A dermoscopic close-up of a skin lesion:
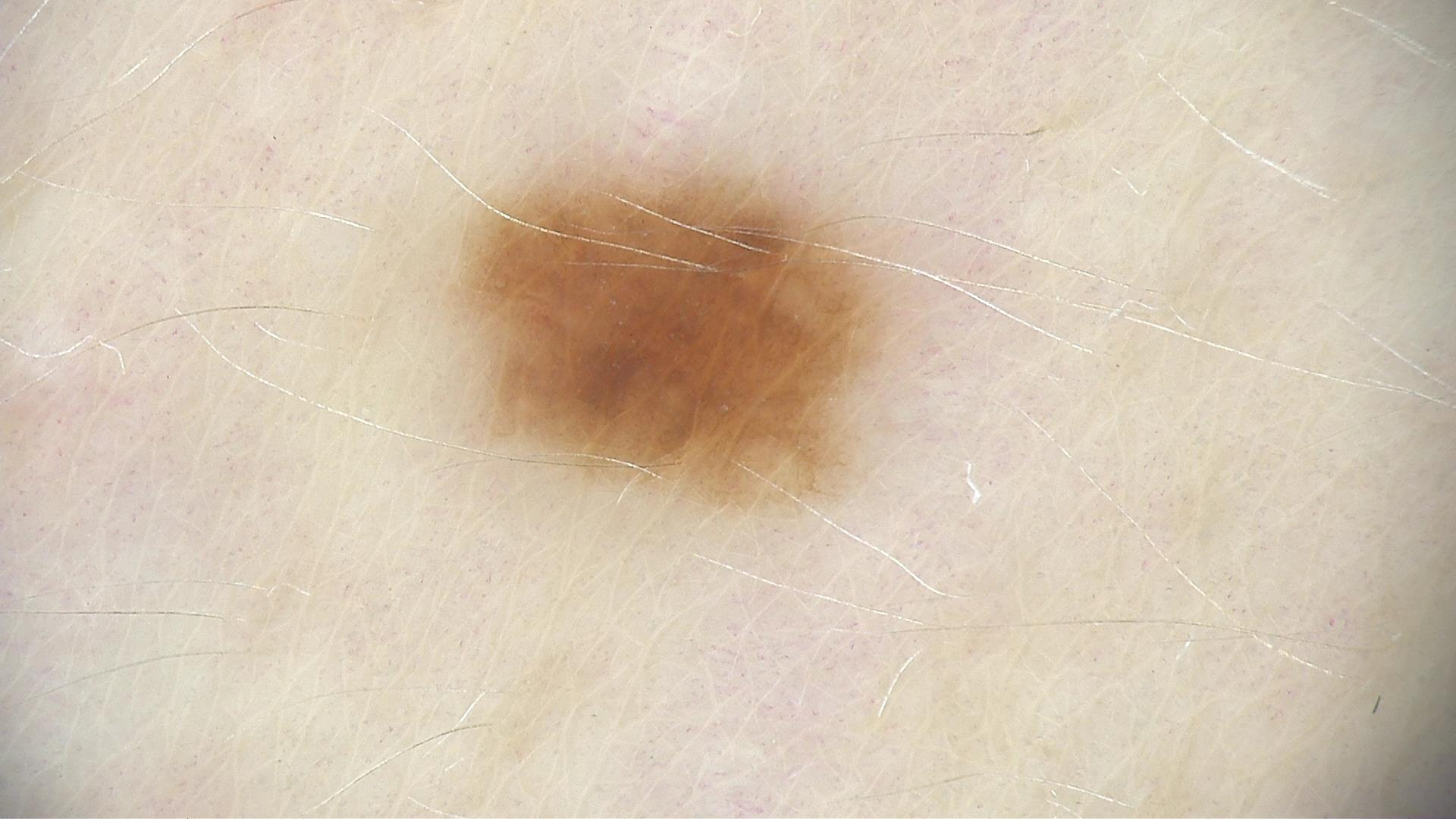Labeled as a benign lesion — a dysplastic junctional nevus.